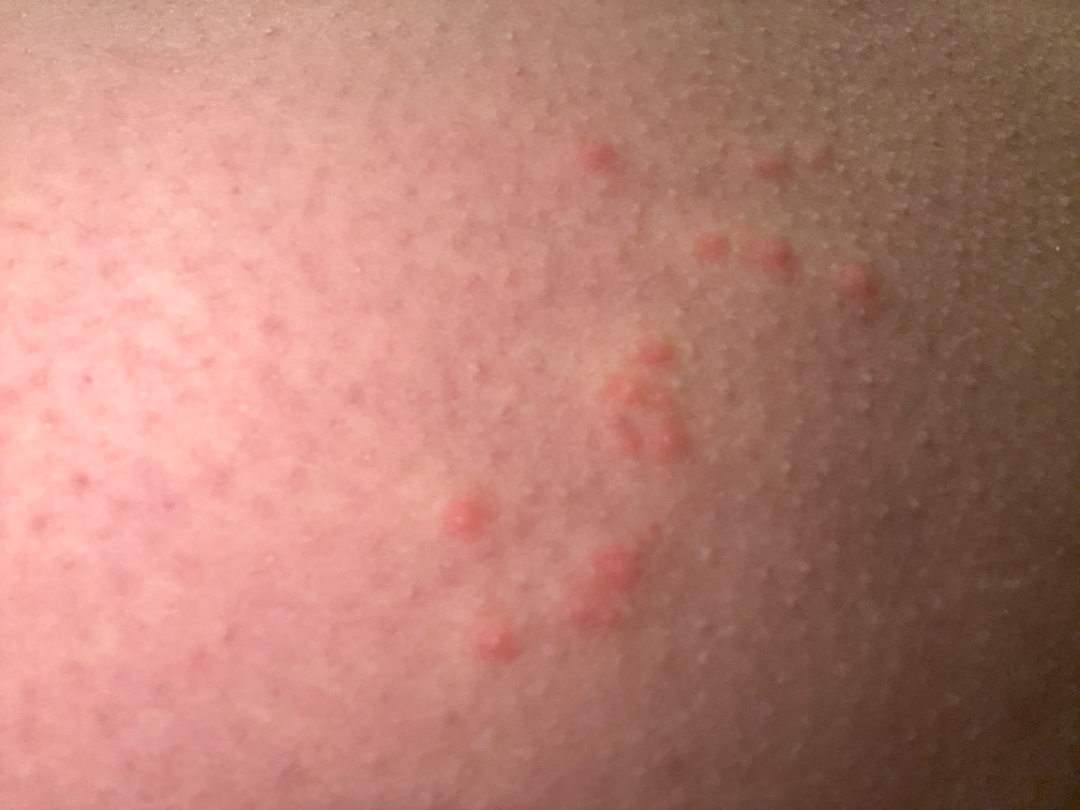subject = female, age 18–29 | body site = leg | photo taken = close-up | diagnostic considerations = single-reviewer assessment: the primary impression is Folliculitis; the differential also includes Miliaria; less probable is Hypersensitivity.